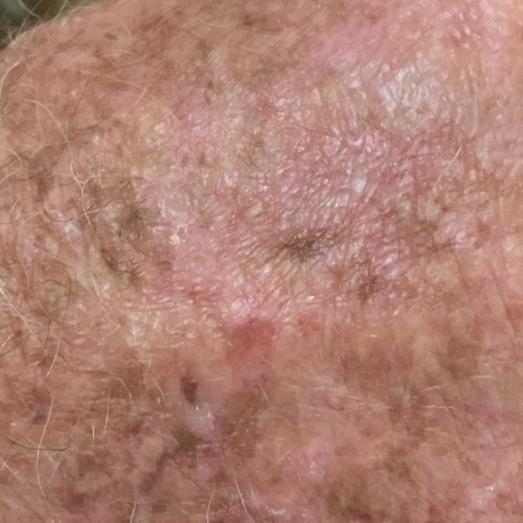{
  "diagnosis": {
    "name": "actinic keratosis",
    "code": "ACK",
    "malignancy": "indeterminate",
    "confirmation": "clinical consensus"
  }
}